The patient is female. No associated systemic symptoms reported. Located on the arm and leg. Skin tone: non-clinician graders estimated a MST of 4. This image was taken at a distance:
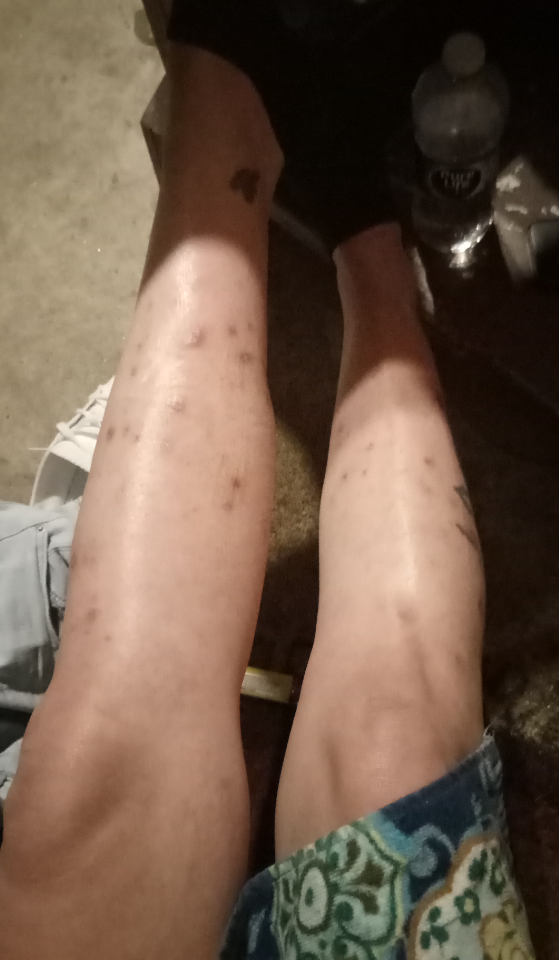Impression: The skin findings could not be characterized from the image.